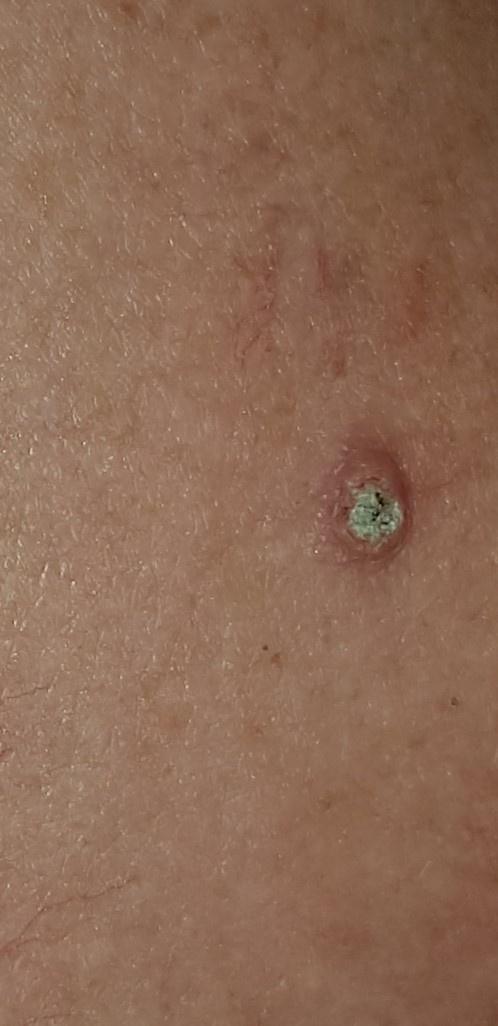FST II.
A female subject roughly 75 years of age.
A clinical photograph showing a skin lesion in context.
The lesion involves the trunk, specifically the posterior trunk.
Biopsy-confirmed as a lesion with uncertain malignant potential — a solar or actinic keratosis.